Skin tone: Fitzpatrick phototype III; the contributor reports itching and bothersome appearance; this image was taken at a distance; the lesion is described as rough or flaky.
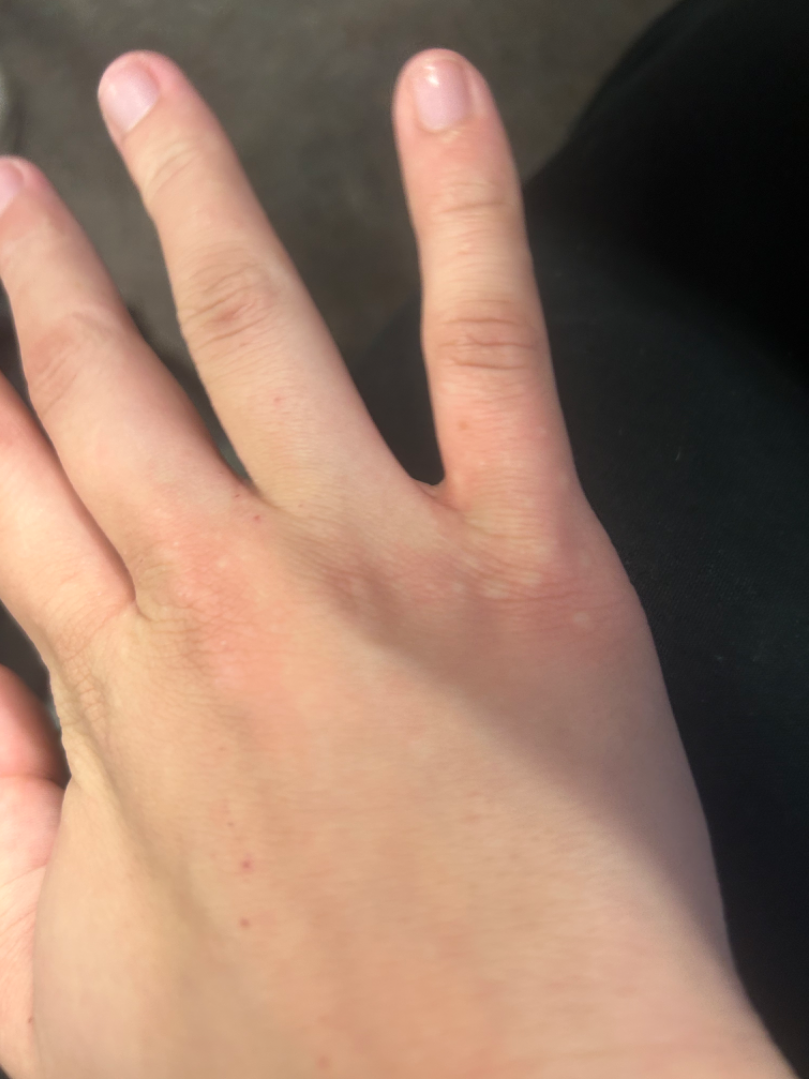dermatologist impression: most consistent with Molluscum Contagiosum; the differential also includes Granuloma annulare; less likely is Keratoderma.